The patient describes having a moderate number of moles · a female patient 50 years old · imaged for a research study, with no referral diagnosis recorded · the patient says their skin reddens painfully with sun exposure:
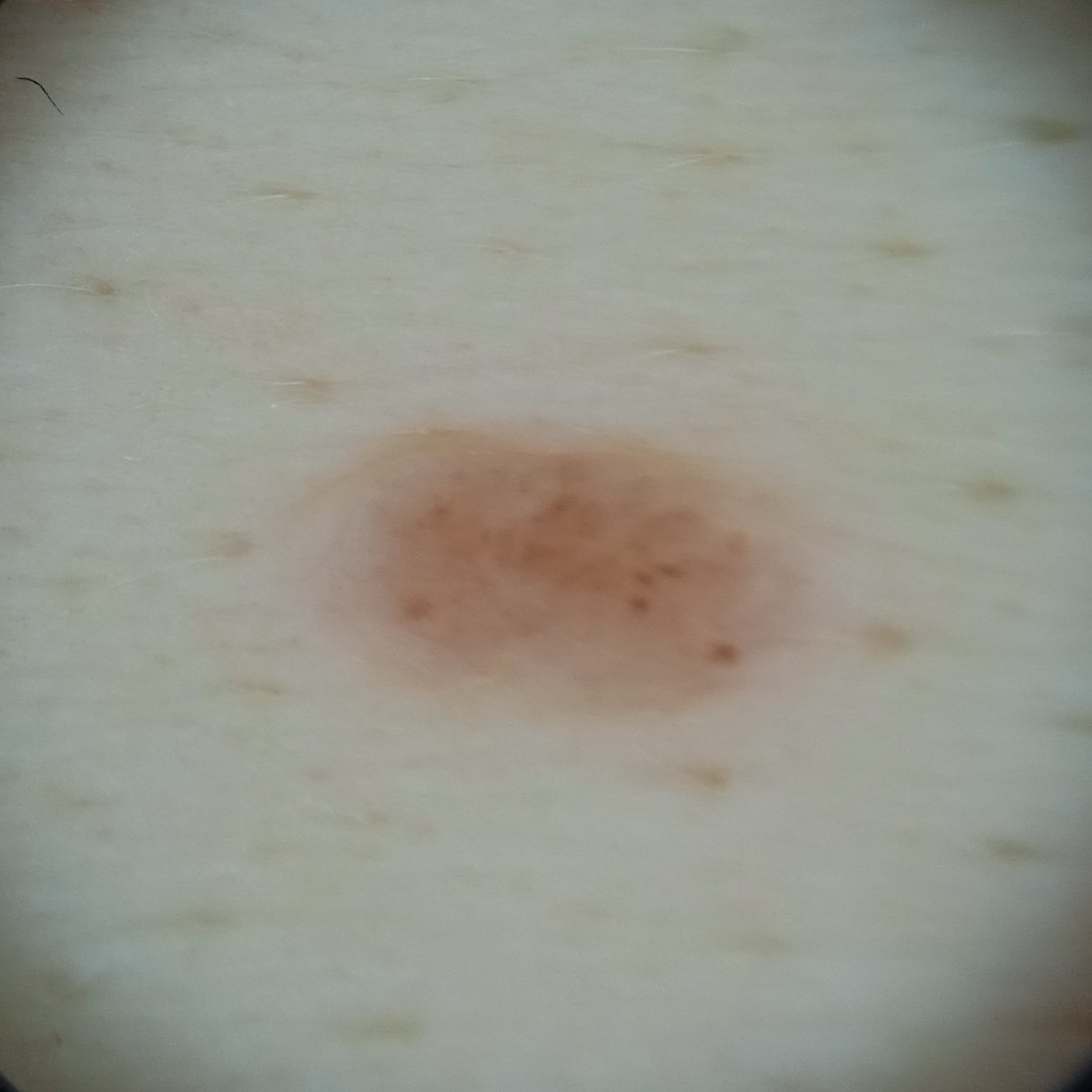• location: the torso
• diameter: 4.9 mm
• diagnosis: melanocytic nevus (dermatologist consensus)